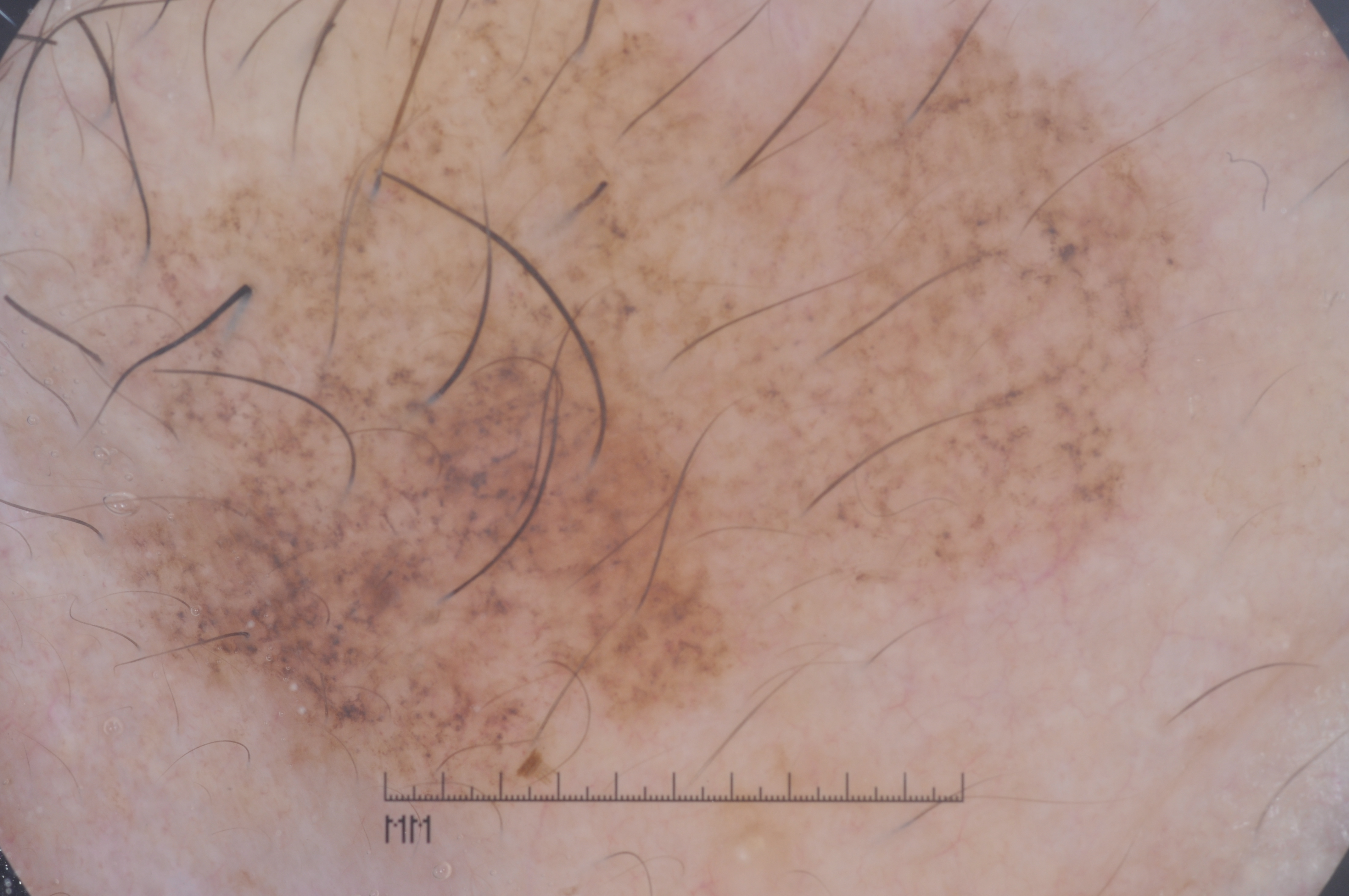Q: What is the imaging modality?
A: dermoscopy
Q: What are the patient's age and sex?
A: male, aged around 70
Q: What does dermoscopy show?
A: milia-like cysts
Q: Where is the lesion located?
A: 63/0/1212/895
Q: What is notable about the lesion's margin?
A: extends past the field edge
Q: What is the diagnosis?
A: a melanoma, a skin cancer